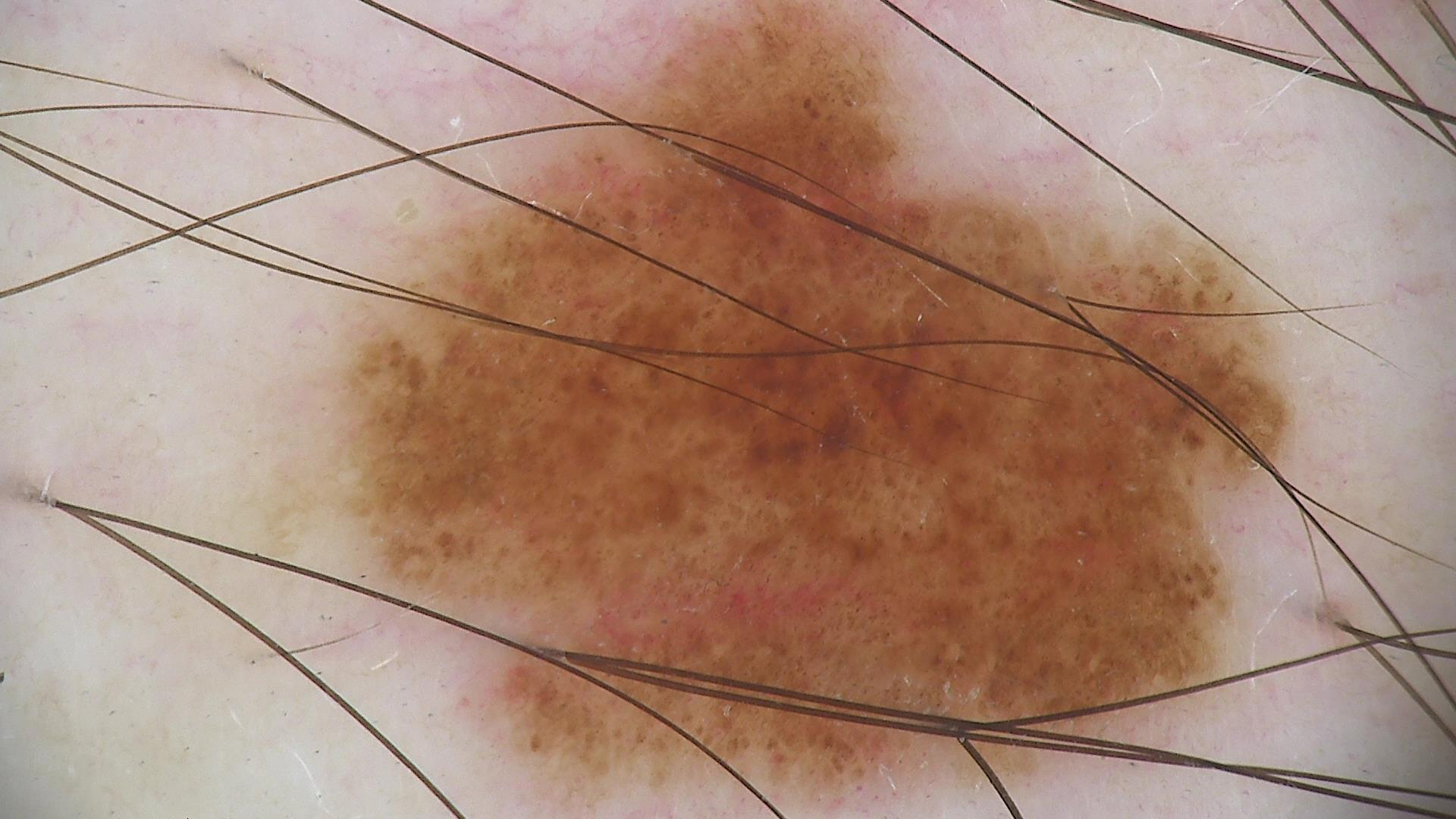modality: dermatoscopy; diagnosis: dysplastic junctional nevus (expert consensus).